A dermoscopic close-up of a skin lesion.
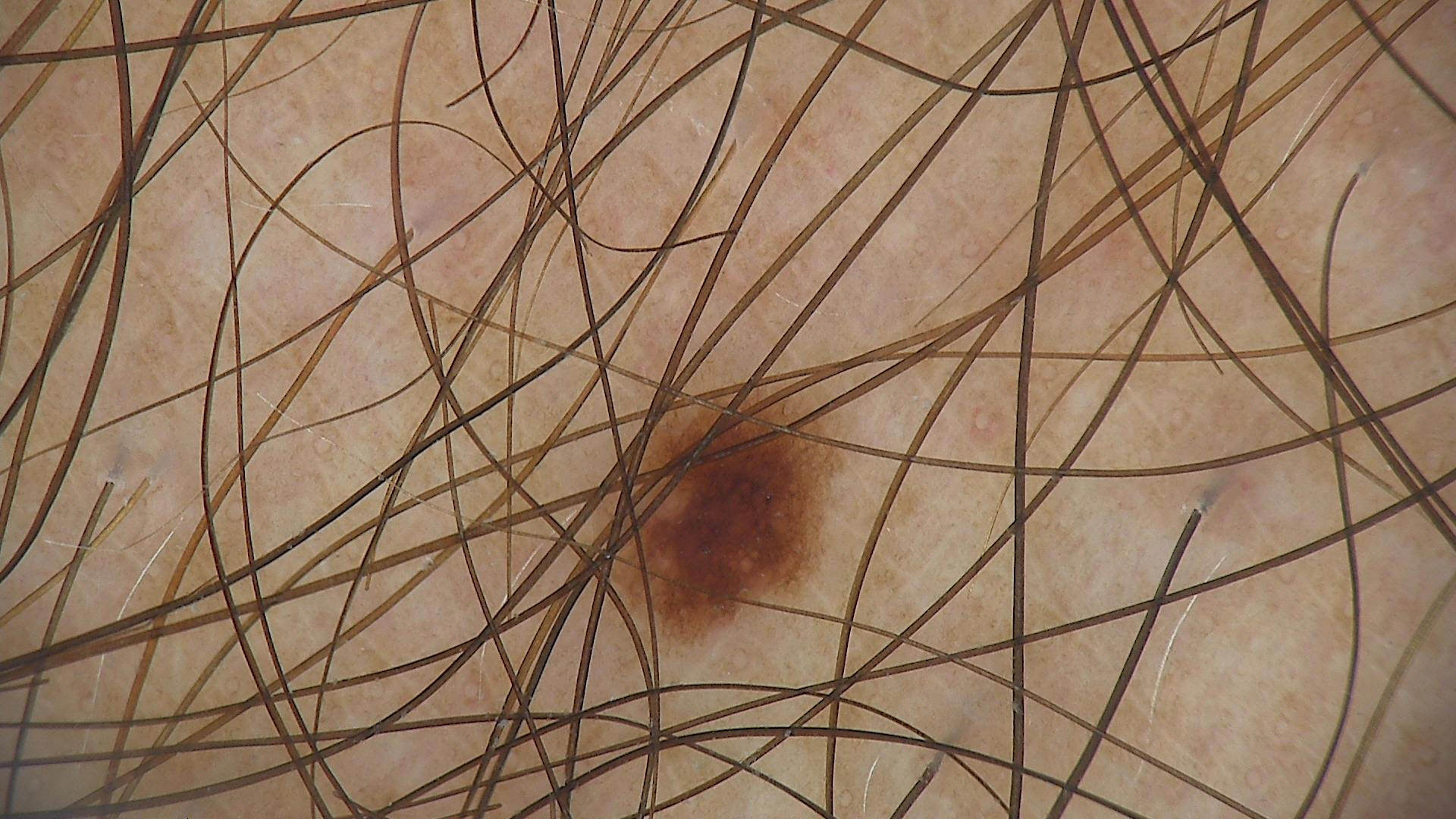Conclusion:
The diagnosis was a dysplastic junctional nevus.